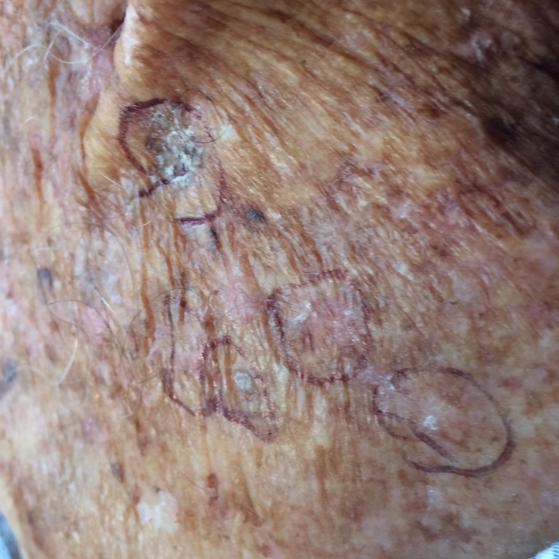Clinically diagnosed as an actinic keratosis.